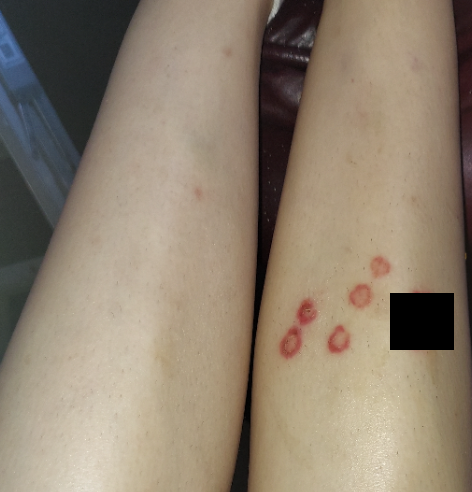Diagnostic features were not clearly distinguishable in this photograph. The patient is a female aged 30–39. The photograph was taken at a distance. The affected area is the leg.